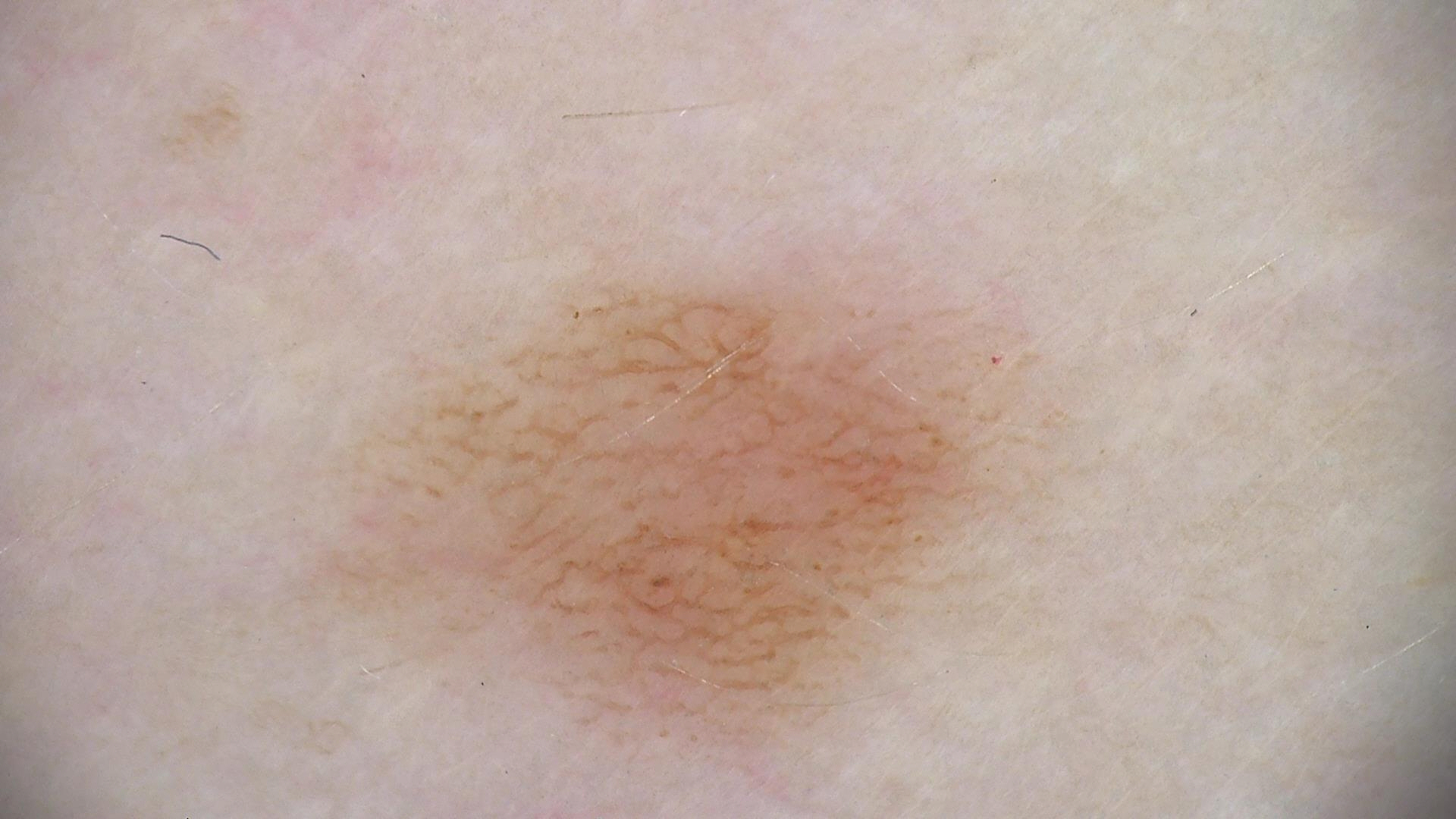The diagnostic label was a banal lesion — a junctional nevus.